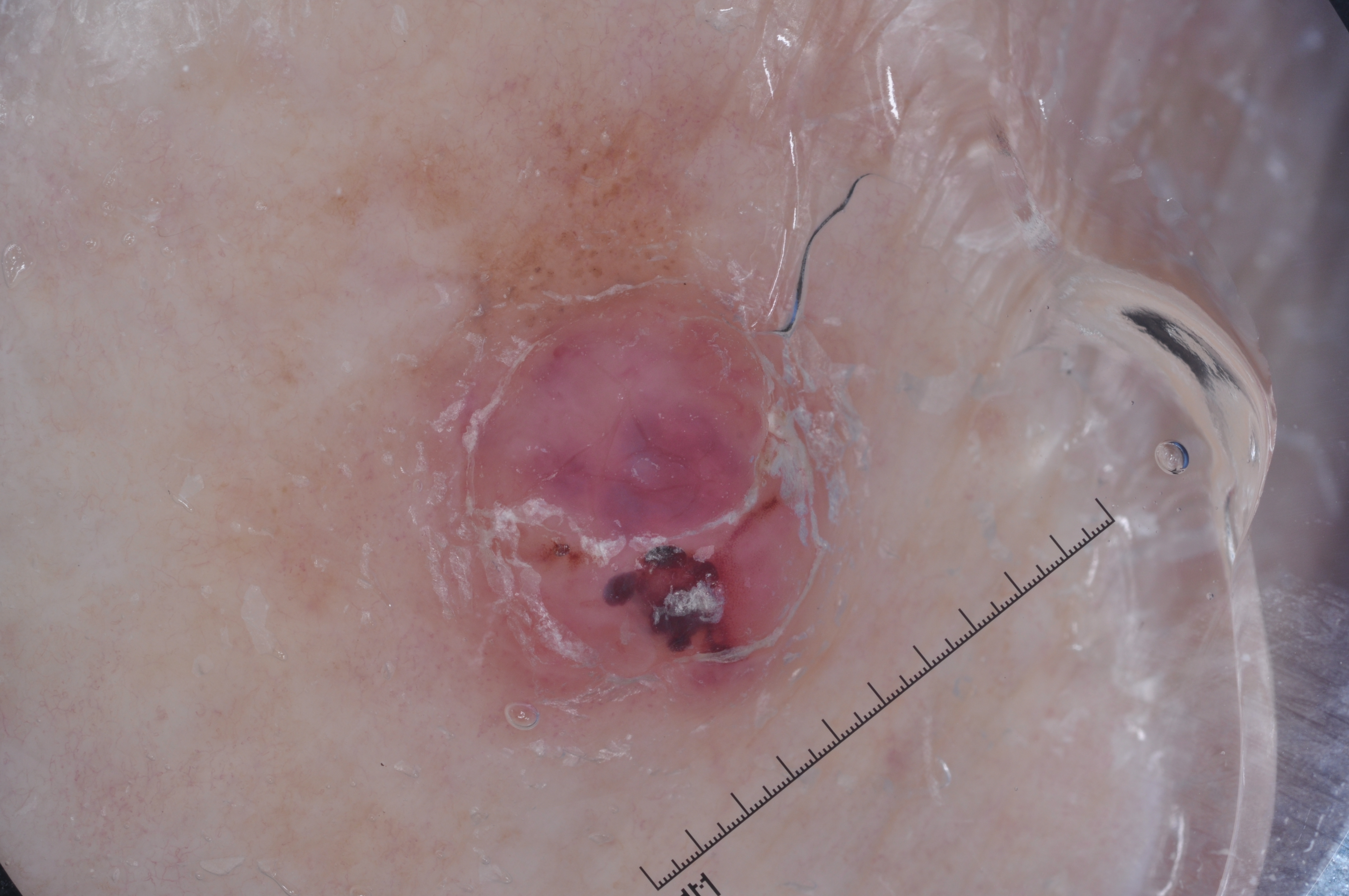A female patient aged 83 or older. A dermoscopic close-up of a skin lesion. Dermoscopic examination shows no streaks, negative network, milia-like cysts, or pigment network. In (x1, y1, x2, y2) order, the lesion is bounded by 410 77 839 733. Histopathology confirmed a melanoma.